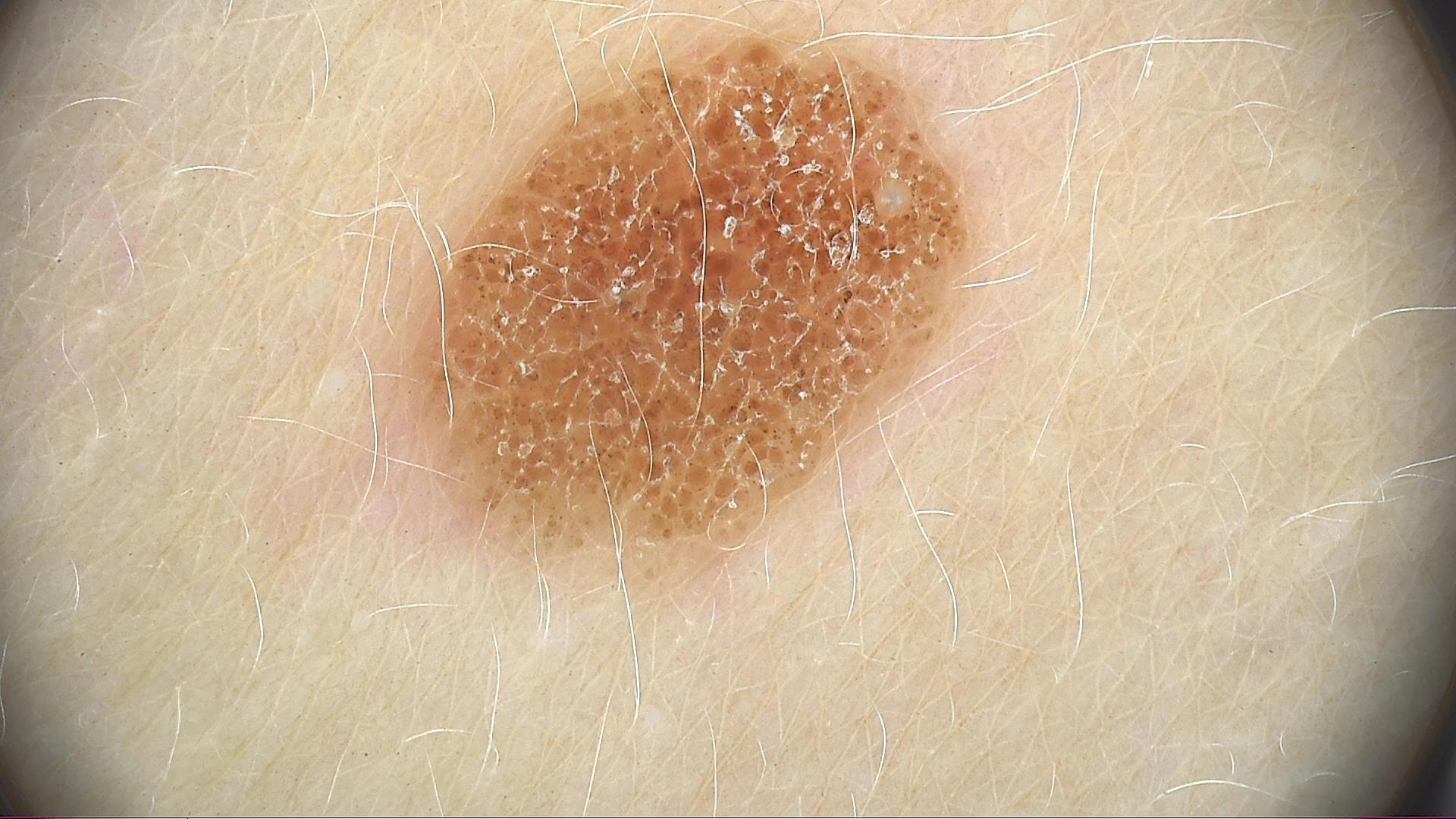Impression: Classified as a compound nevus.